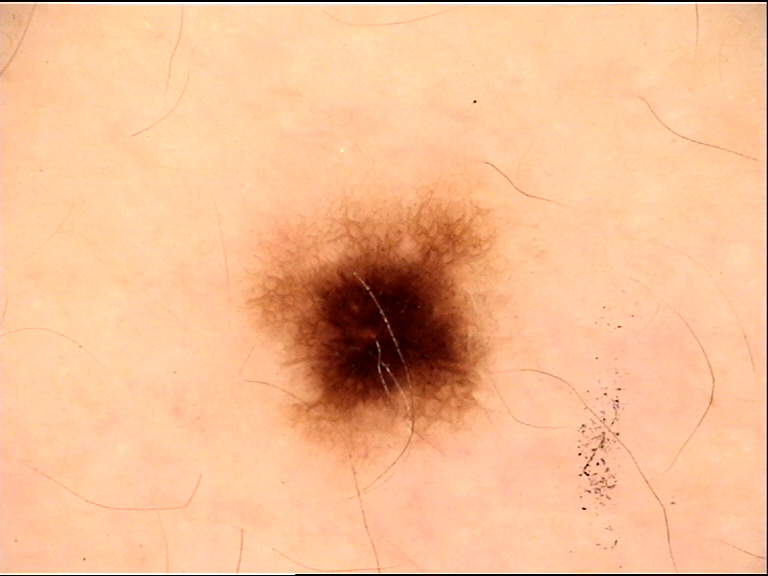image: dermatoscopy
diagnosis:
  name: junctional nevus
  code: jb
  malignancy: benign
  super_class: melanocytic
  confirmation: expert consensus